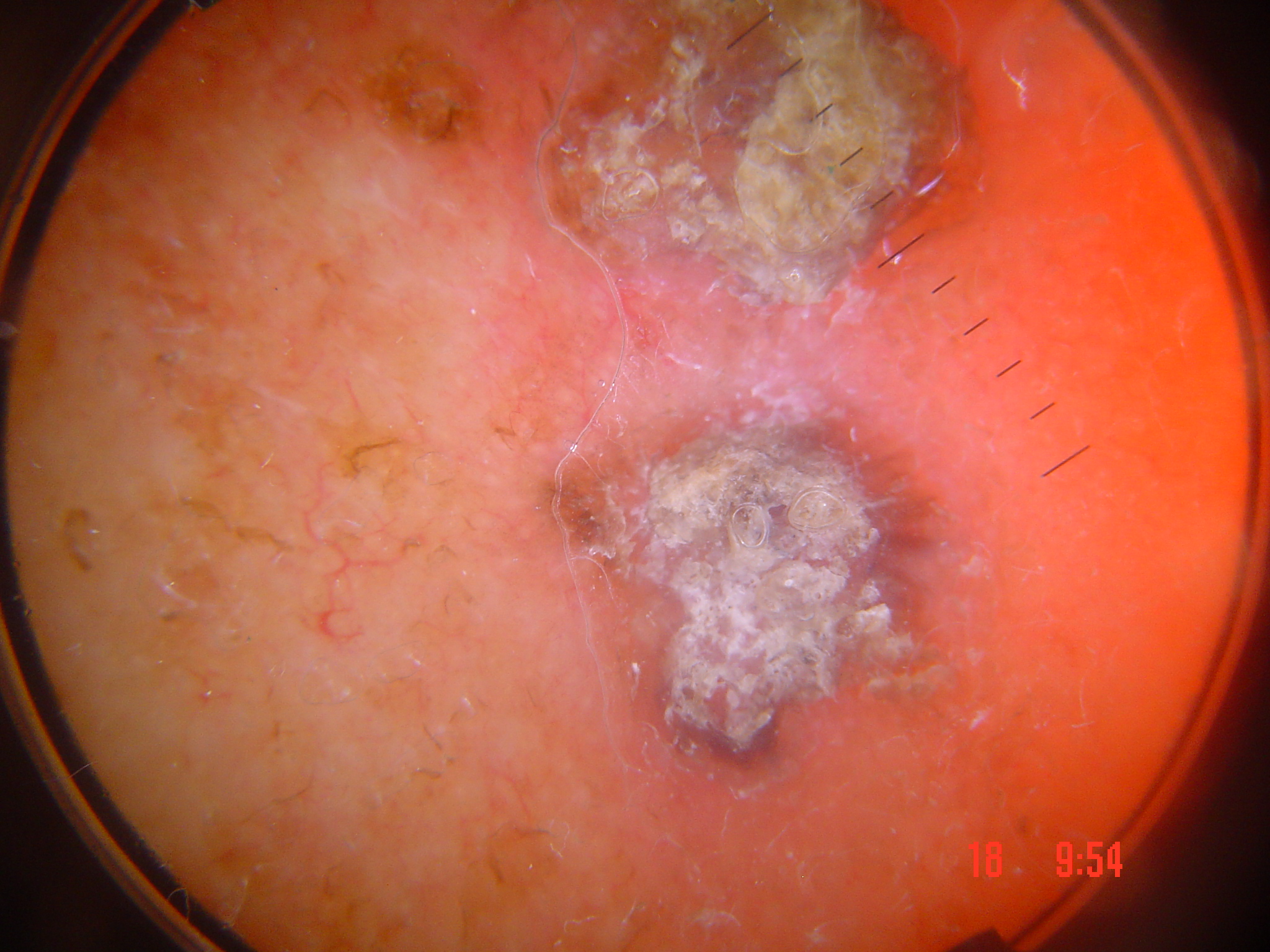A dermatoscopic image of a skin lesion. This is a keratinocytic lesion. Histopathology confirmed a malignancy — a squamous cell carcinoma.